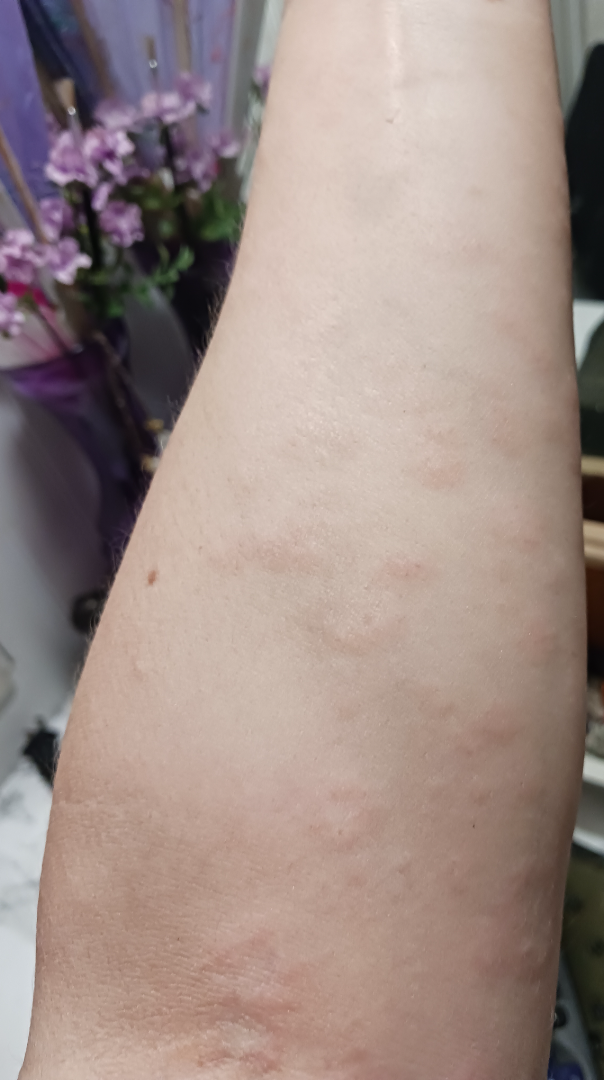Q: Could the case be diagnosed?
A: not assessable